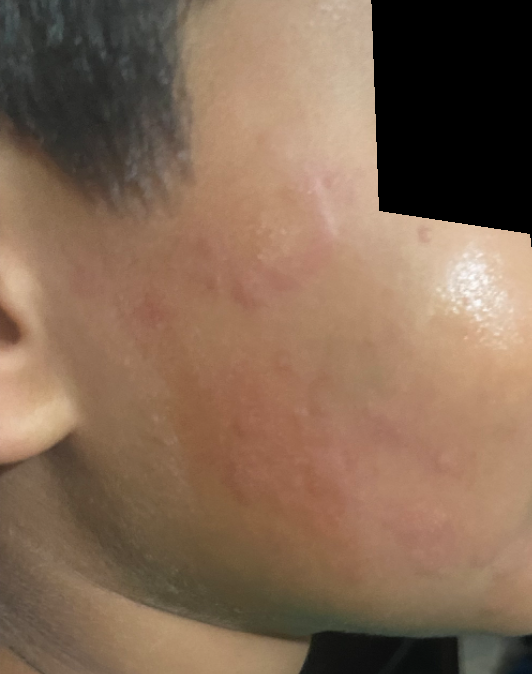Findings:
Reviewed remotely by one dermatologist: favoring Eczema; with consideration of Urticaria.